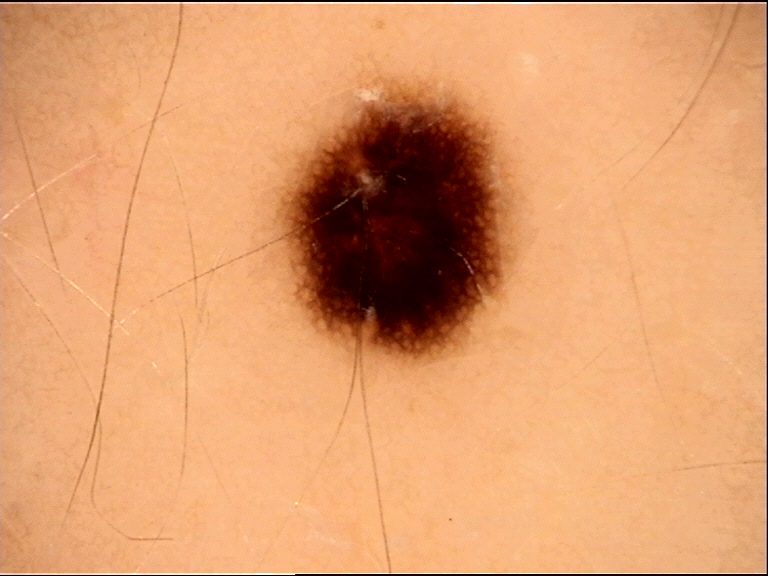Dermoscopy of a skin lesion.
The morphology is that of a banal lesion.
Classified as a junctional nevus.